A dermoscopic view of a skin lesion; the subject is a female aged approximately 55:
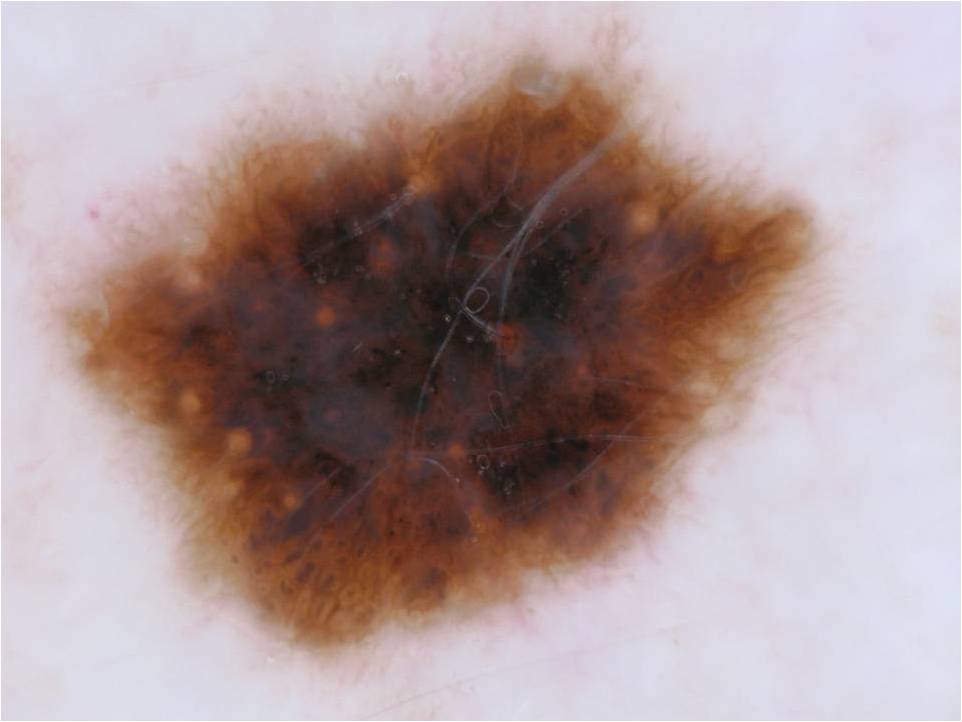A large lesion occupying much of the field.
The lesion is bounded by (31, 14, 838, 683).
On dermoscopy, the lesion shows globules, streaks, and pigment network.
Diagnosed as a melanocytic nevus.